Dermoscopy of a skin lesion: 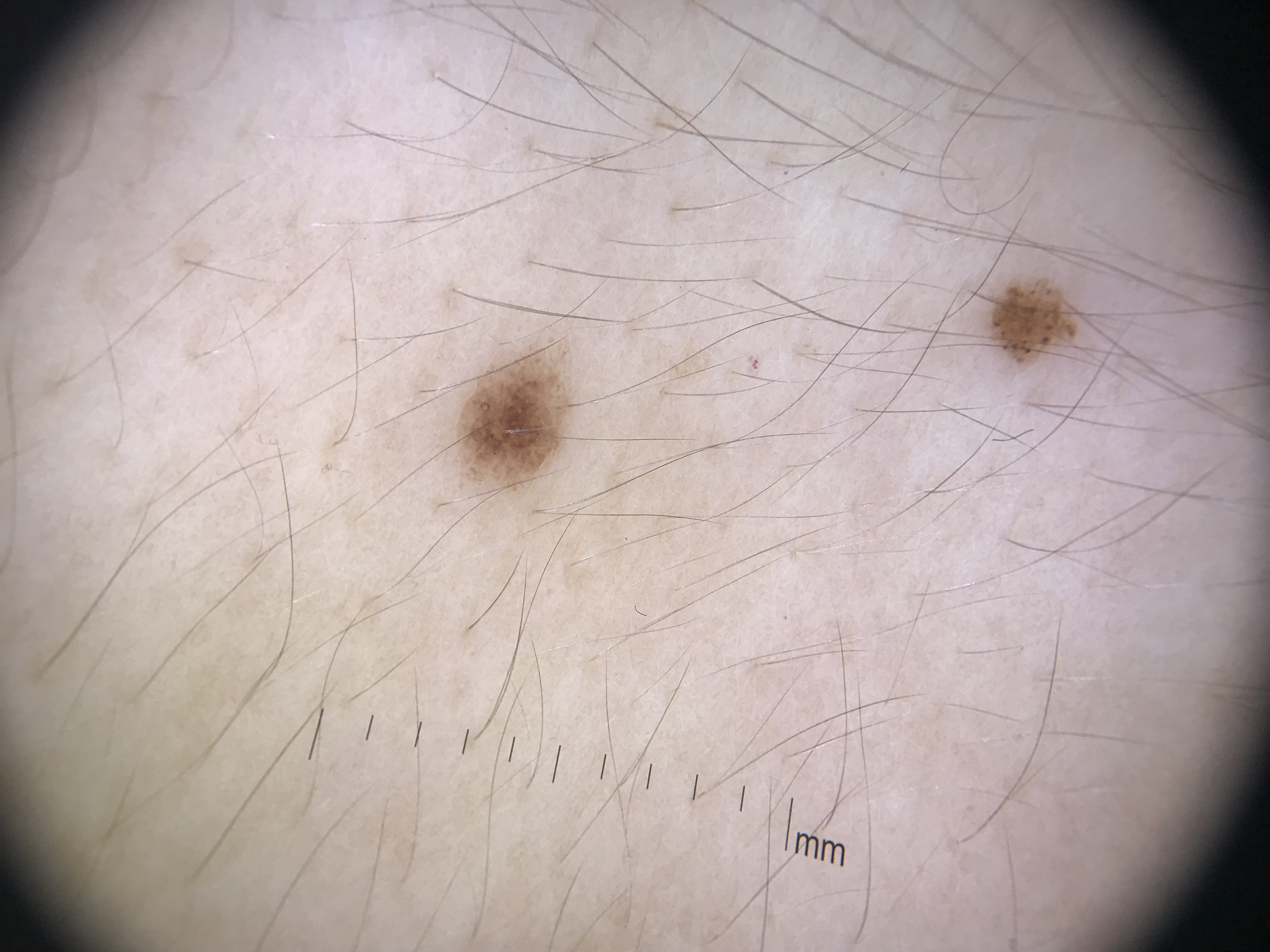Consistent with a banal lesion — a junctional nevus.